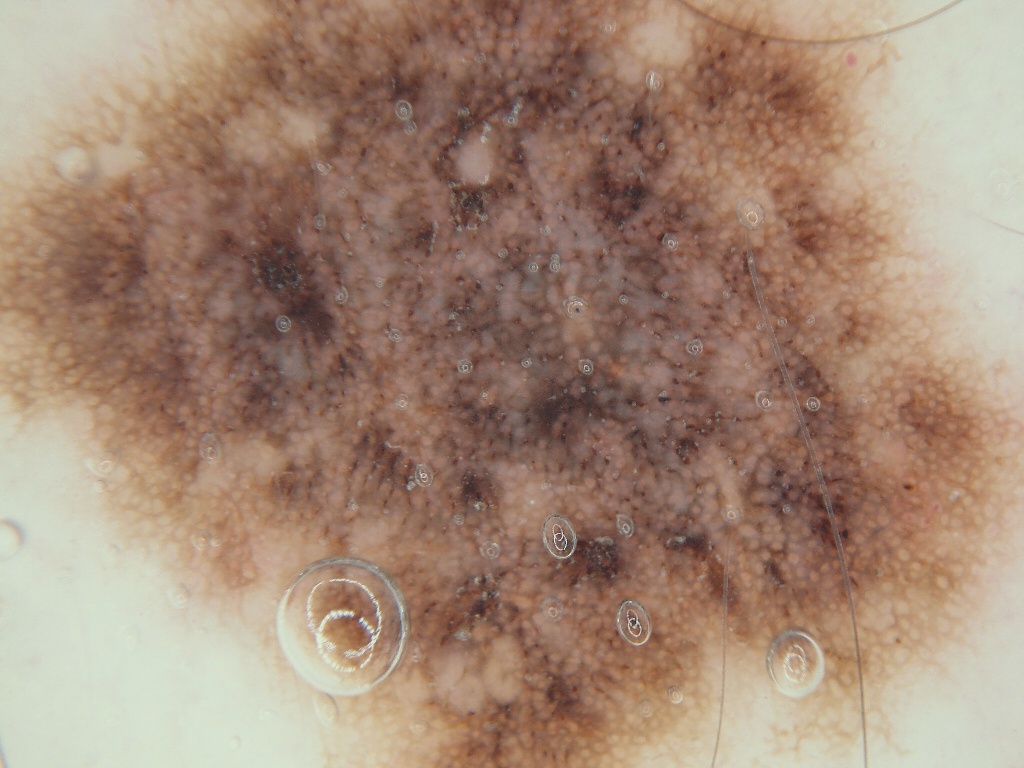Findings:
A dermatoscopic image of a skin lesion. The lesion reaches across nearly the entire image.
Impression:
The lesion was assessed as a benign lesion.